Close-up view; located on the leg, front of the torso and arm: 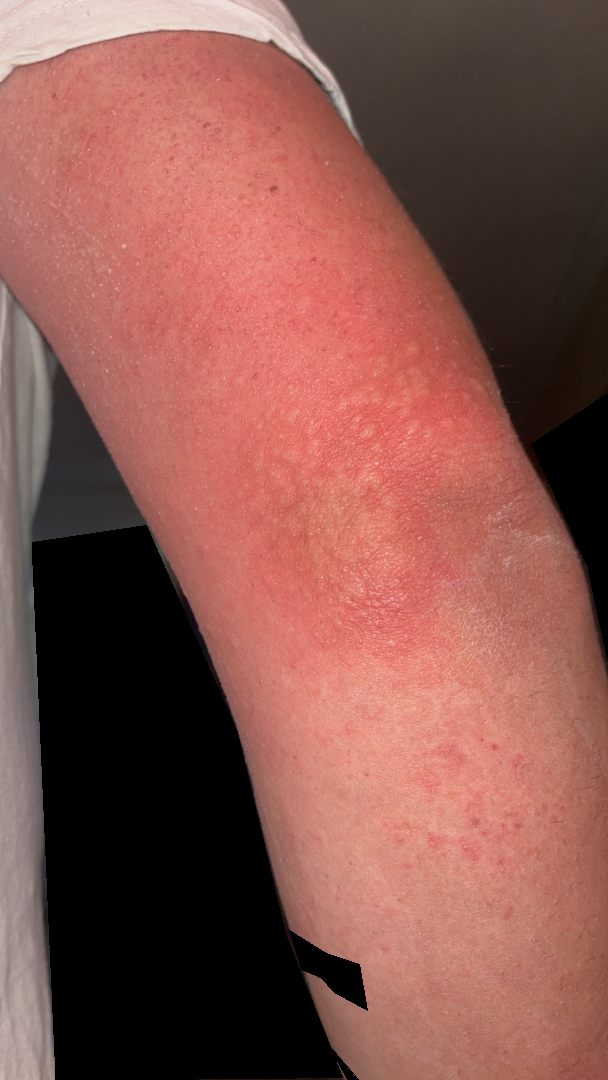diagnostic considerations — consistent with Urticaria